A contact-polarized dermoscopy image of a skin lesion · a male patient in their 80s · the patient was assessed as Fitzpatrick II.
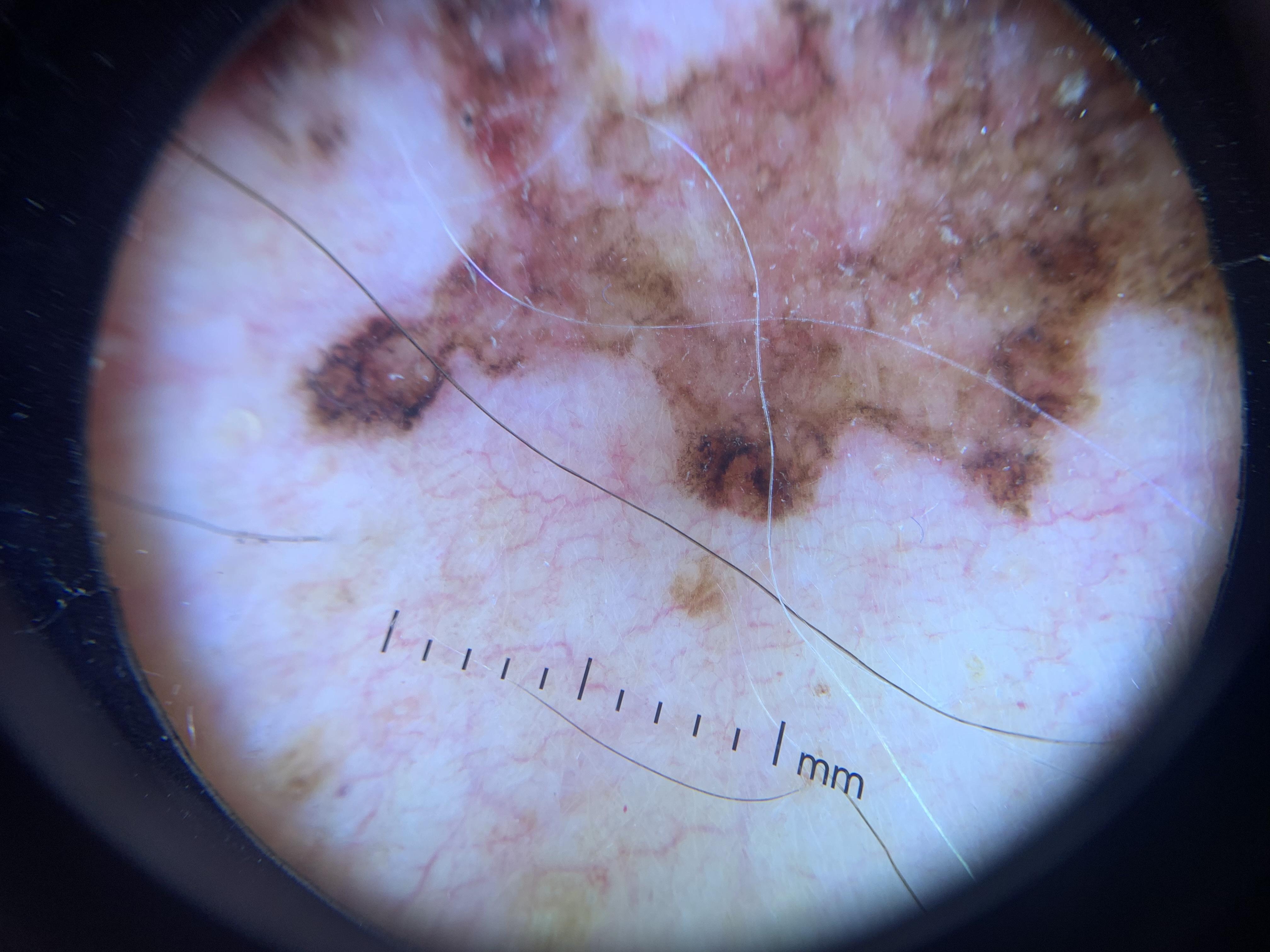location=the trunk (the anterior trunk) | diagnosis=Melanoma (biopsy-proven).